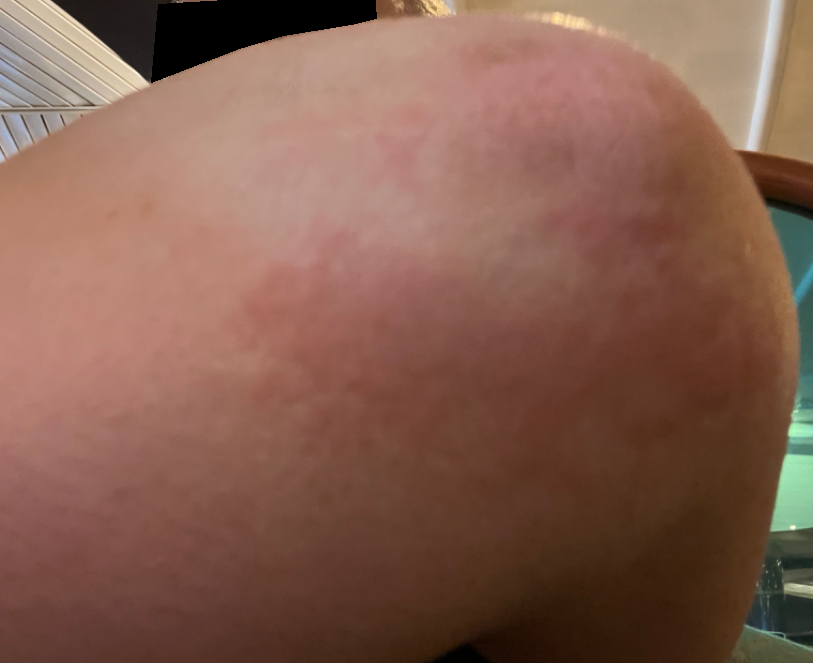skin tone = lay reviewers estimated Monk skin tone scale 2 or 3 (two reviewer pools) | anatomic site = arm | subject = female, age 40–49 | photo taken = close-up | reported symptoms = itching | texture = raised or bumpy | self-categorized as = a rash | symptom duration = less than one week | differential = three independent reviewers: the favored diagnosis is Allergic Contact Dermatitis; also raised was Urticaria; also consider Eczema; a remote consideration is Dermatitis herpetiformis.